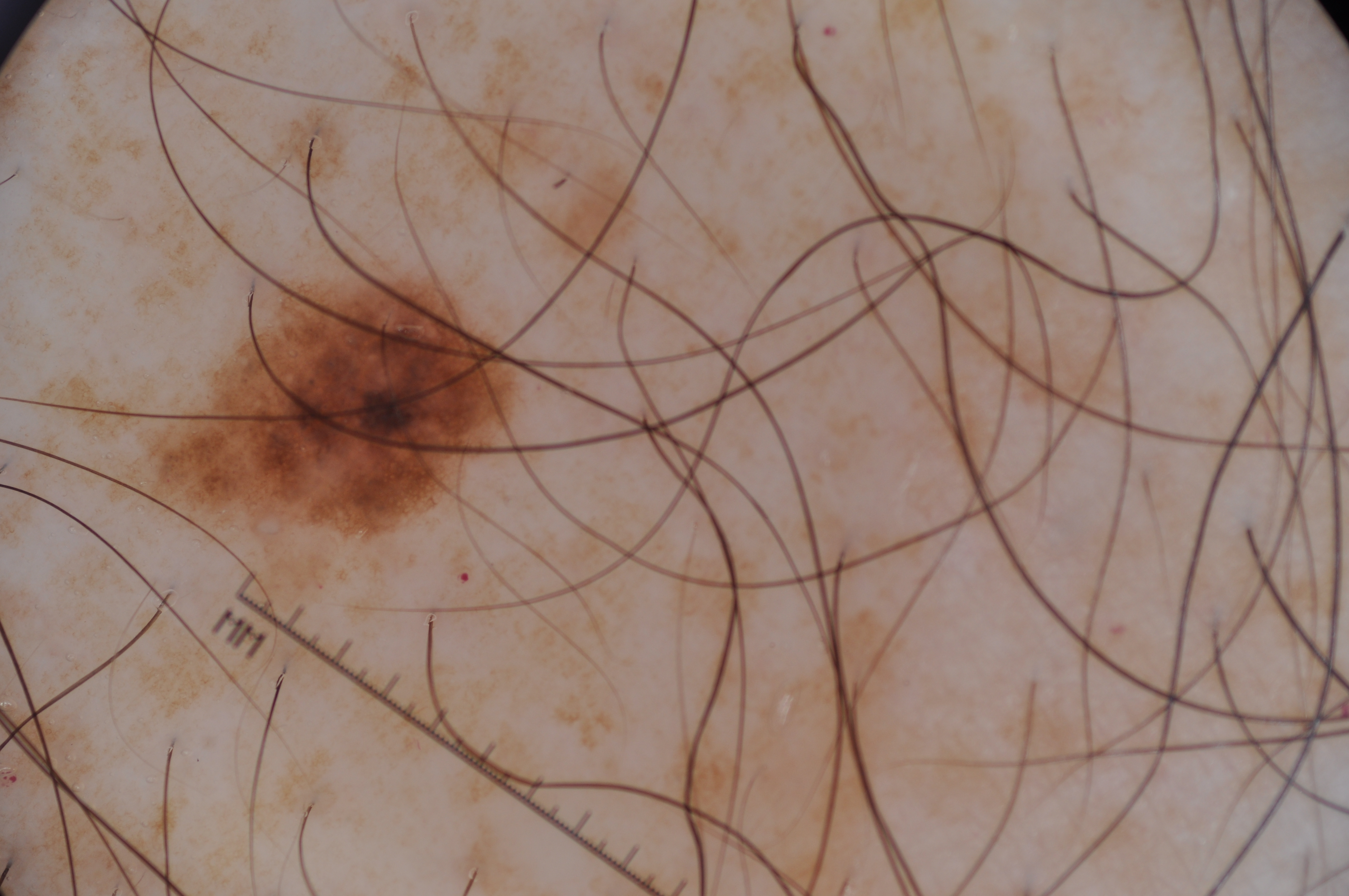The patient is a male aged 58-62. Dermoscopy of a skin lesion. In (x1, y1, x2, y2) order, the lesion is located at (147, 273, 517, 532). Dermoscopic review identifies pigment network, with no streaks, milia-like cysts, or negative network. The lesion is small relative to the field of view. Clinically diagnosed as a melanocytic nevus, a benign lesion.